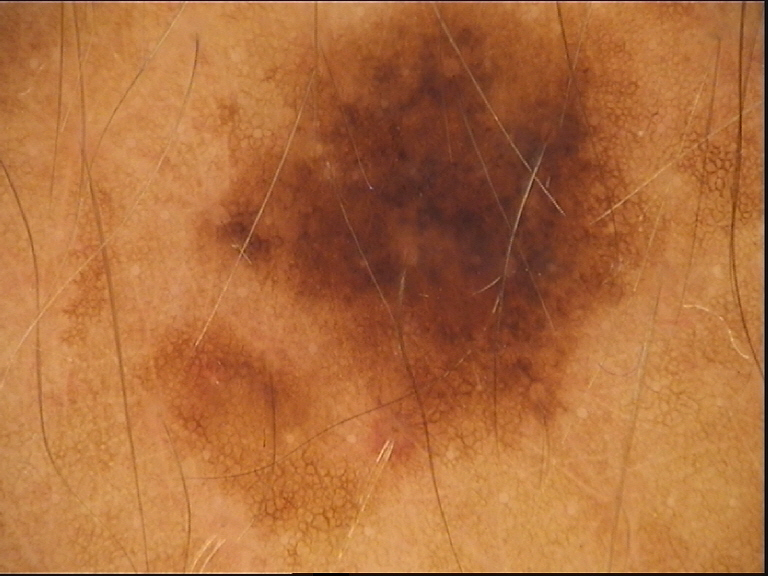Q: What kind of image is this?
A: dermoscopy
Q: What is the diagnosis?
A: dysplastic compound nevus (expert consensus)